A clinical photograph showing a skin lesion; a male subject in their early 60s; the patient is Fitzpatrick skin type III.
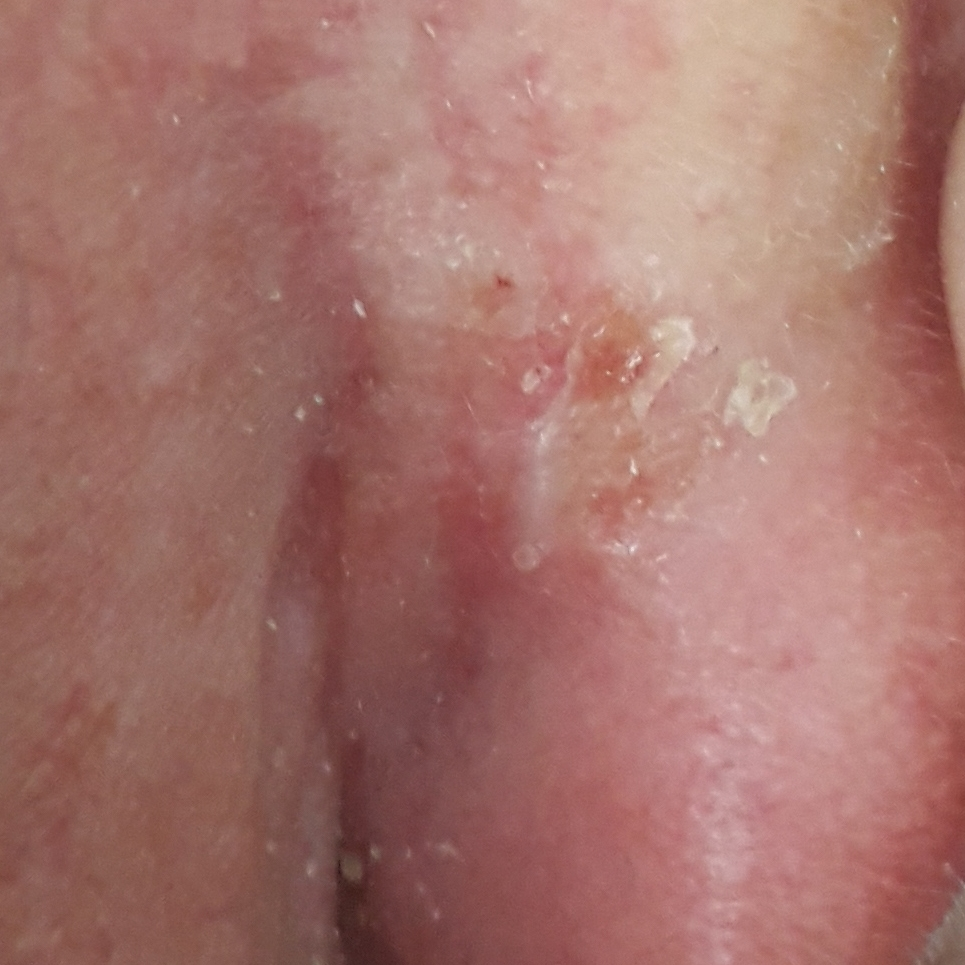{"lesion_location": "an ear", "lesion_size": {"diameter_1_mm": 6.0, "diameter_2_mm": 6.0}, "symptoms": "none reported", "diagnosis": {"name": "basal cell carcinoma", "code": "BCC", "malignancy": "malignant", "confirmation": "histopathology"}}